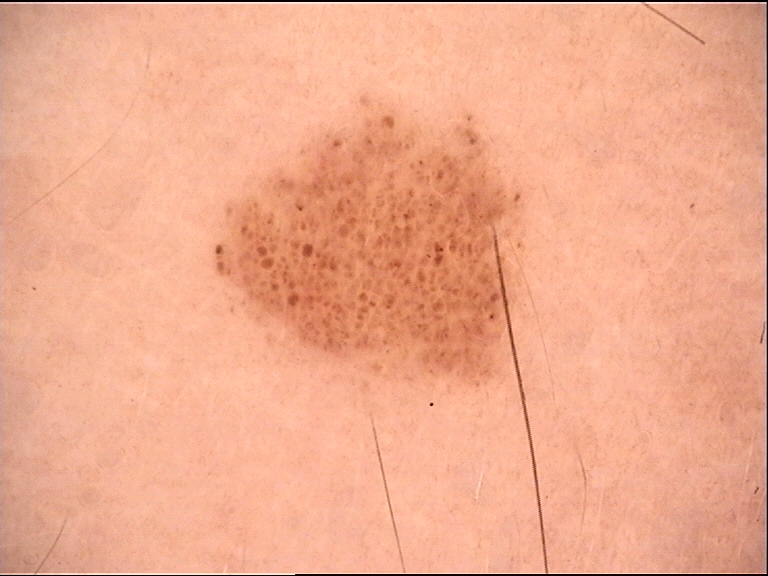Conclusion: Diagnosed as a dysplastic junctional nevus.